A dermatoscopic image of a skin lesion:
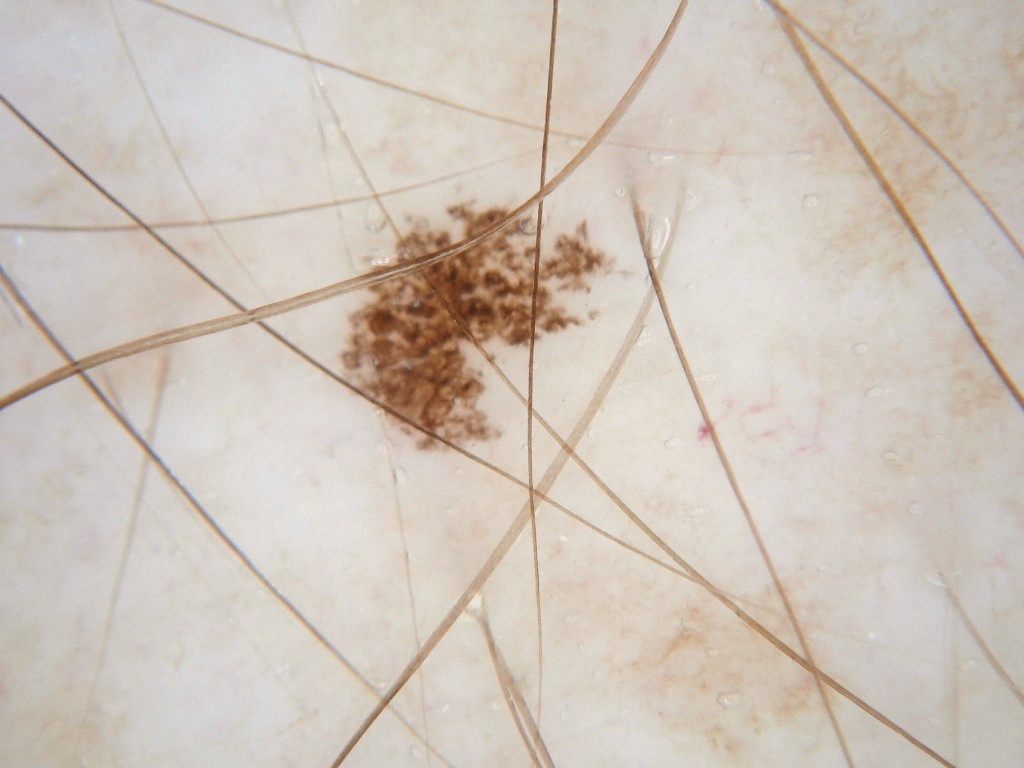* lesion location: <bbox>313, 179, 640, 476</bbox>
* absent dermoscopic features: streaks and globules
* impression: a benign lesion